A clinical photograph of a skin lesion; the patient was assessed as Fitzpatrick skin type II — 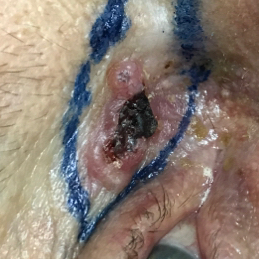Findings:
- location — the face
- patient-reported symptoms — elevation, itching, bleeding
- pathology — basal cell carcinoma (biopsy-proven)